A dermatoscopic image of a skin lesion:
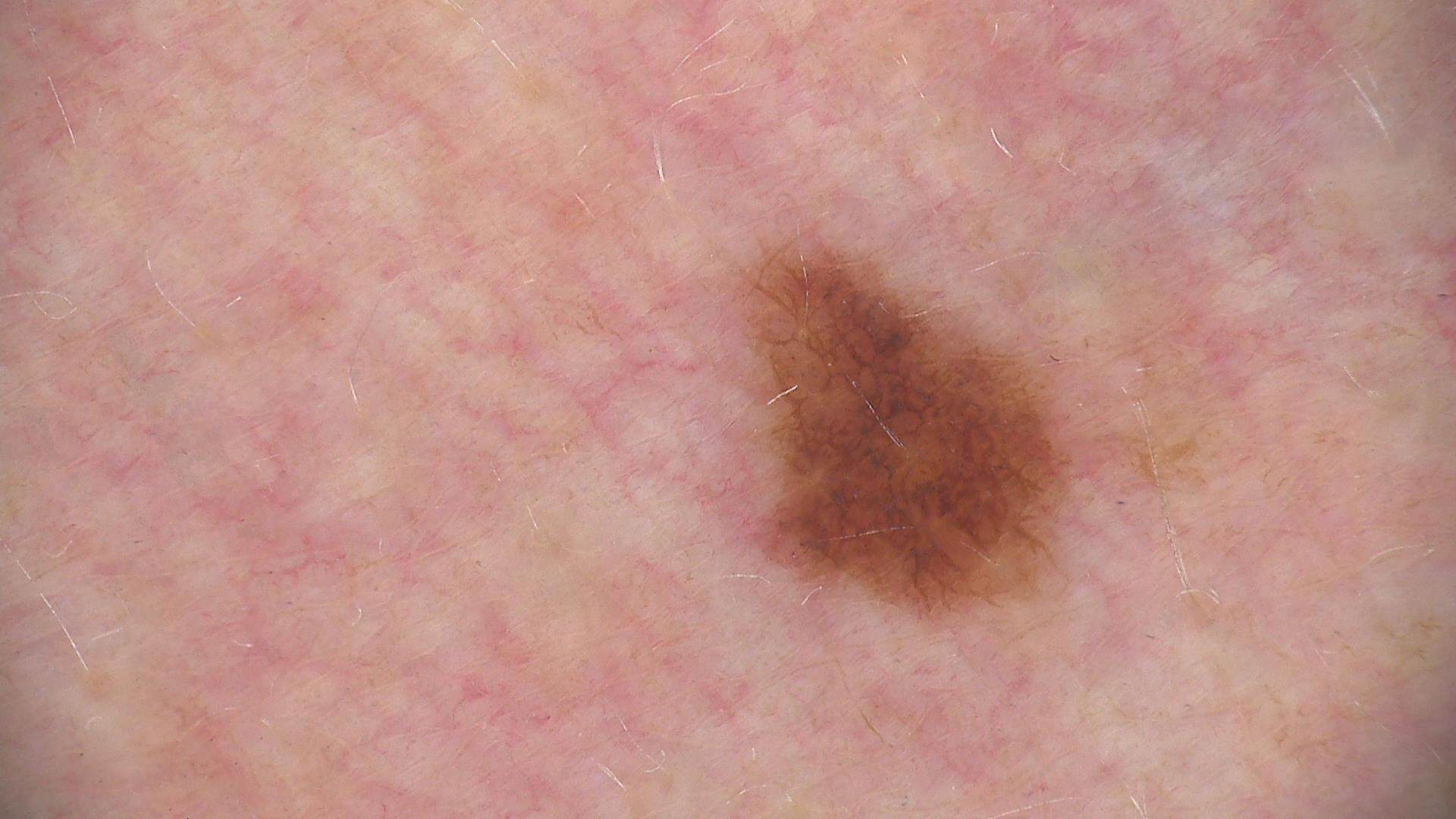Findings:
* assessment: dysplastic junctional nevus (expert consensus)